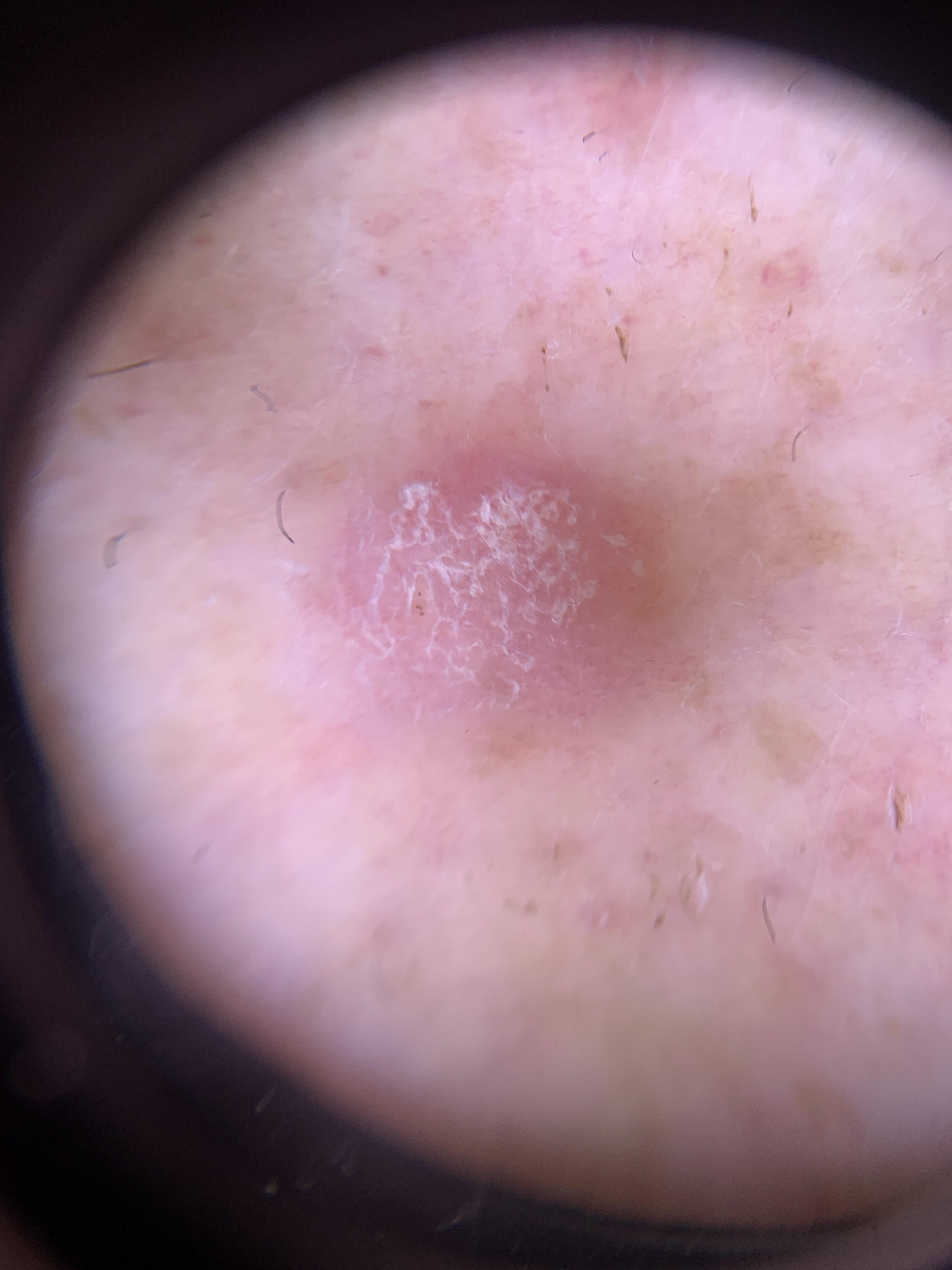modality: contact-polarized dermoscopy | Fitzpatrick: I | patient: female, roughly 75 years of age | body site: a lower extremity | pathology: Solar or actinic keratosis (biopsy-proven).